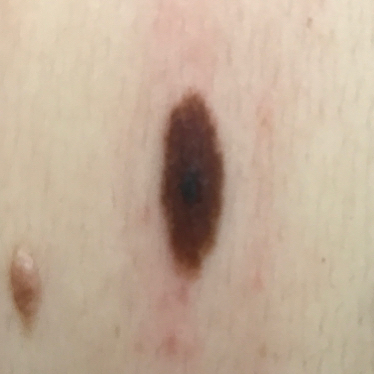Q: What are the relevant risk factors?
A: prior skin cancer (patient or family), prior malignancy (patient or family)
Q: What is the imaging modality?
A: clinical photograph
Q: Skin phototype?
A: II
Q: Tell me about the patient.
A: female, in their early 30s
Q: What is the anatomic site?
A: the back
Q: How large is the lesion?
A: 7x3 mm
Q: What does the patient describe?
A: no pain, no itching
Q: What did the workup show?
A: nevus (biopsy-proven)